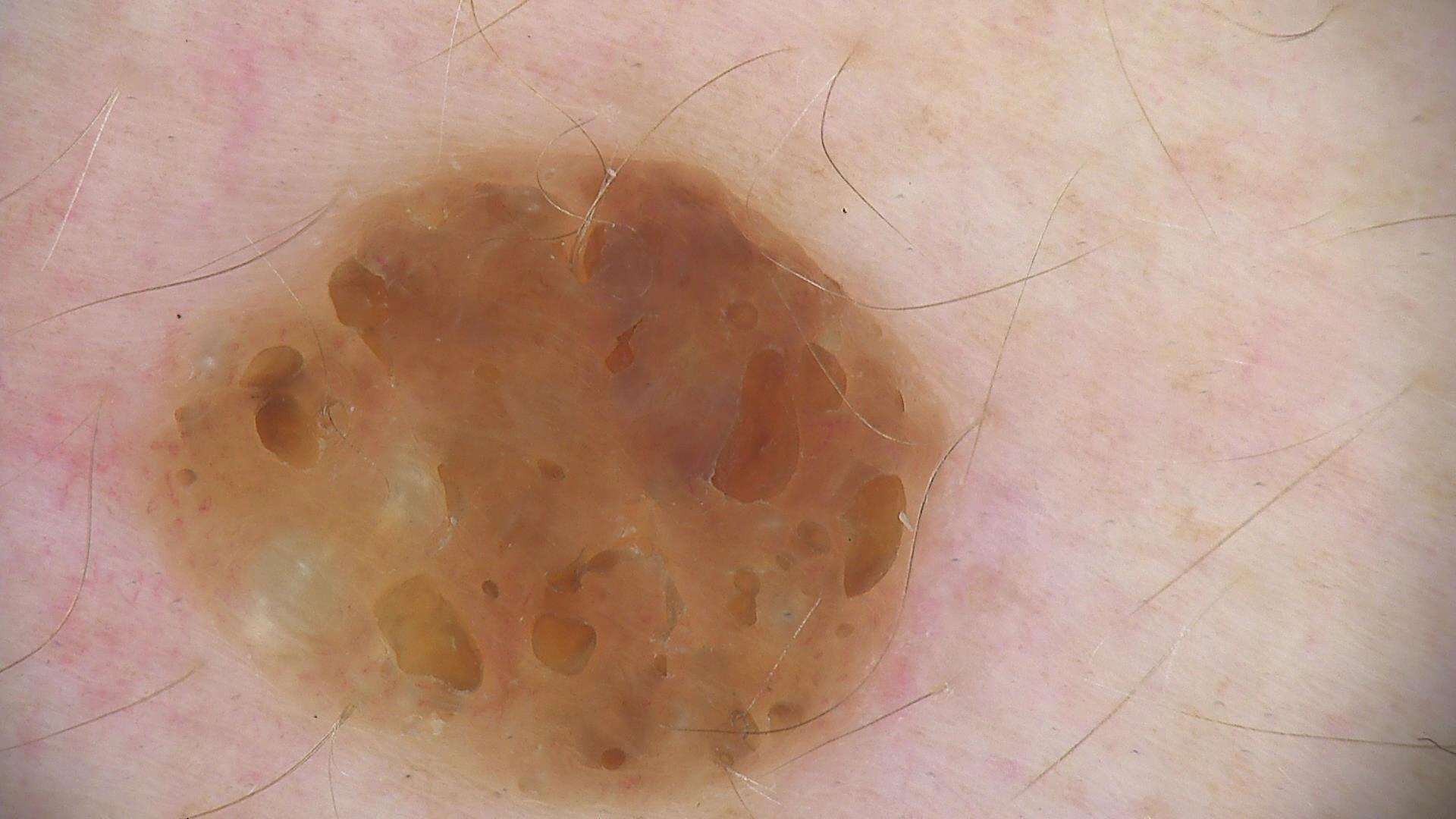Impression:
Classified as a seborrheic keratosis.